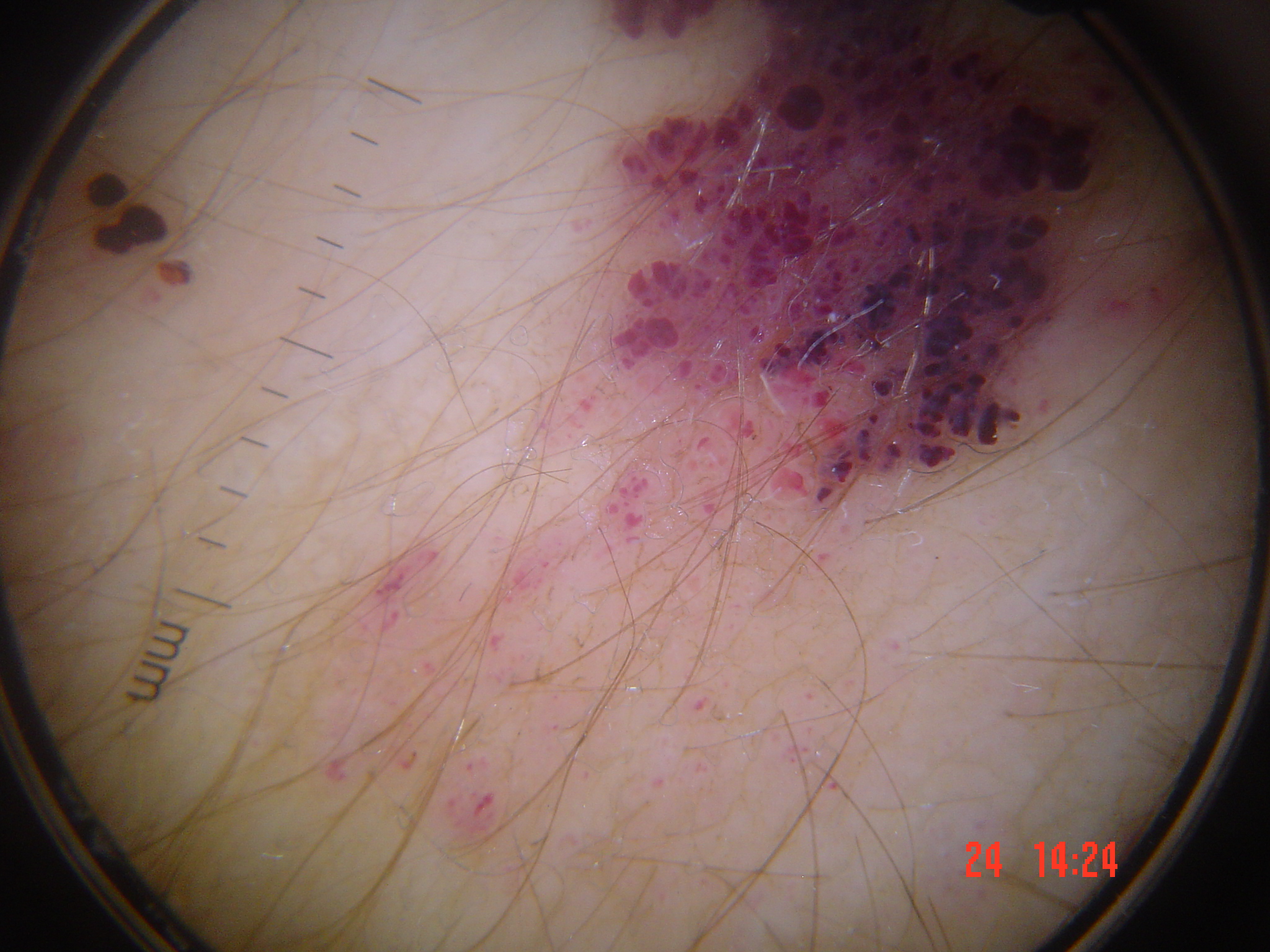Findings:
- imaging — dermoscopy
- assessment — angiokeratoma (expert consensus)